The affected area is the arm, the patient described the issue as a rash, the photograph was taken at a distance.
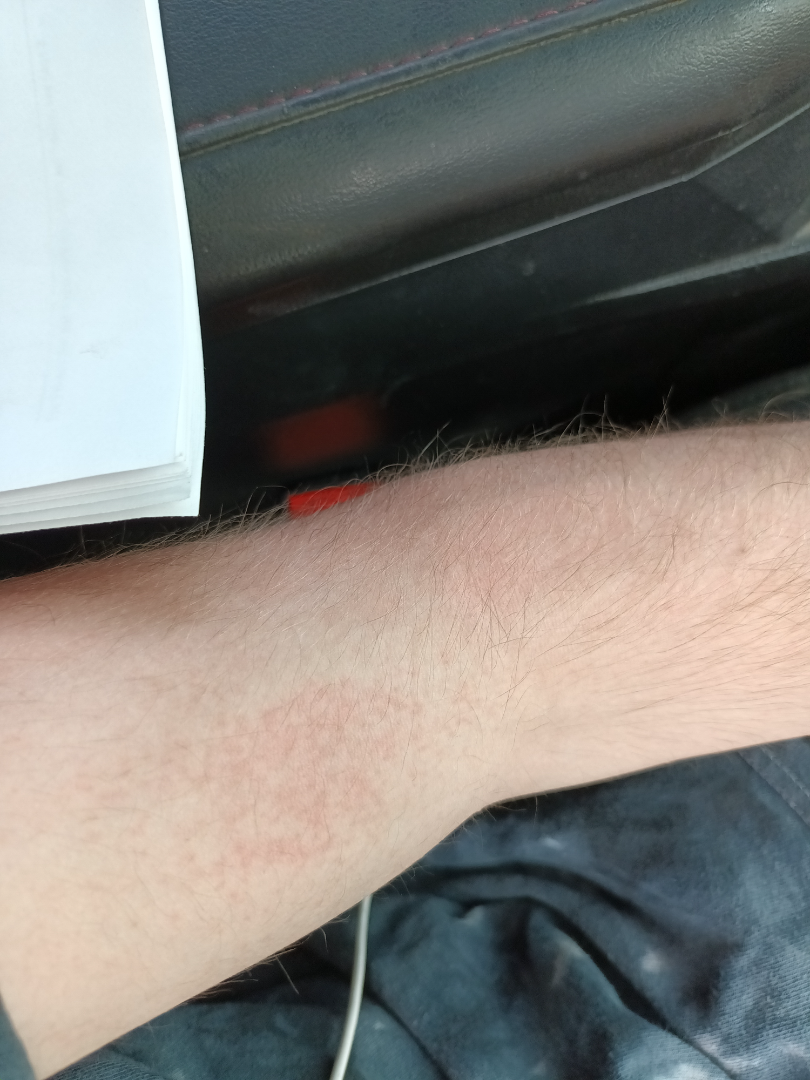Assessment:
No differential diagnosis could be assigned on photographic review.